Recorded as Fitzpatrick skin type III; a male patient in their 40s:
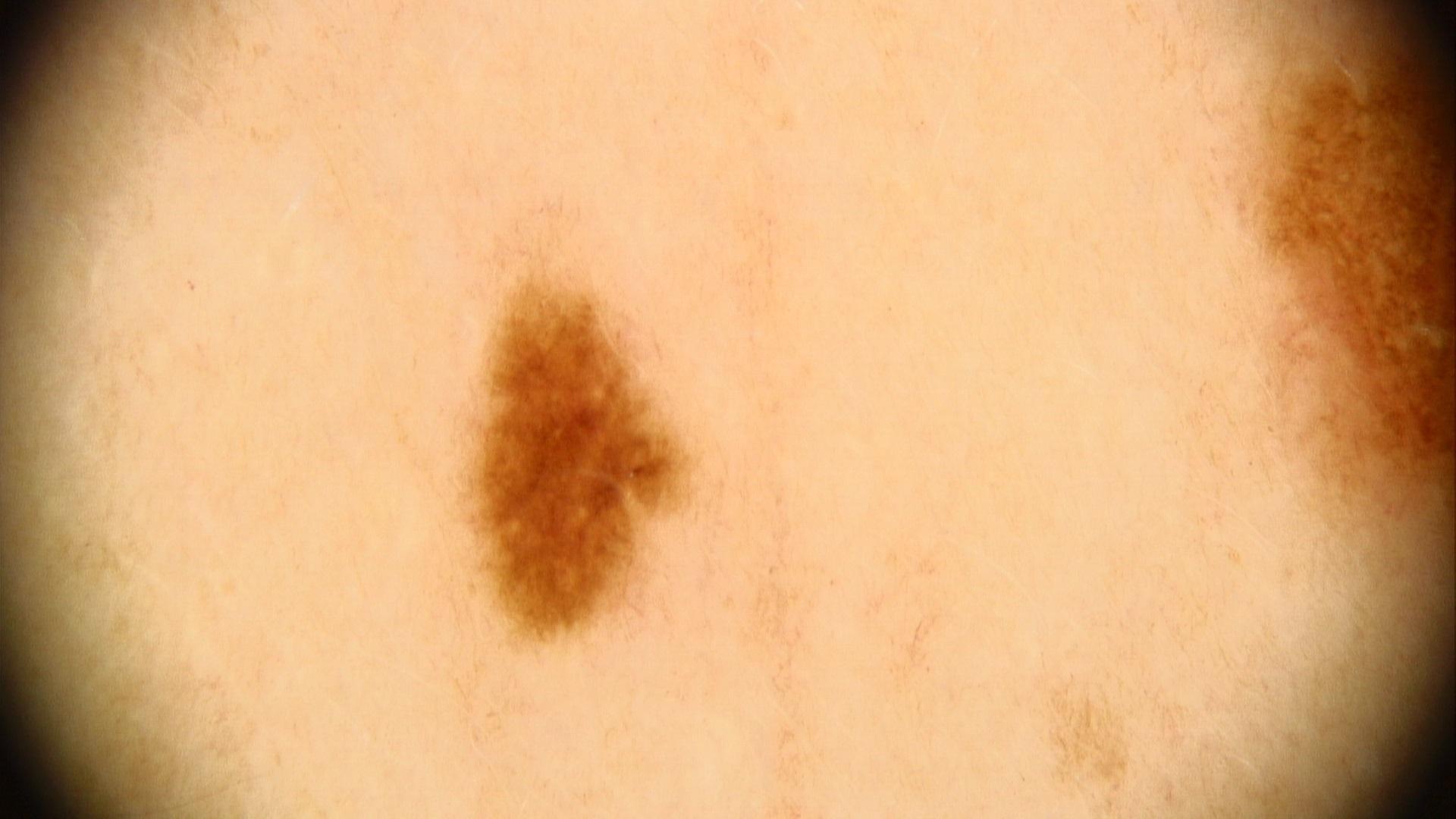Located on the posterior trunk. The diagnostic impression was a lesion of melanocytic origin — a nevus.